The photo was captured at an angle: 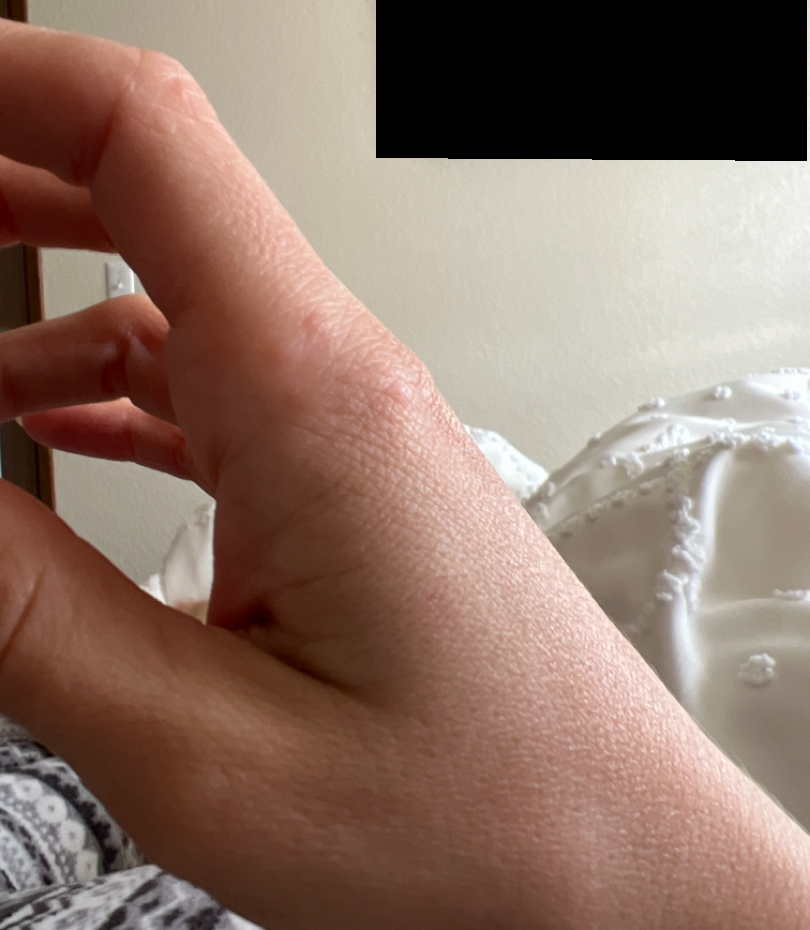Skin tone: Fitzpatrick III; lay reviewers estimated a MST of 2. On photographic review: the leading impression is Insect Bite; the differential also includes Urticaria; also raised was Allergic Contact Dermatitis.